The patient is a female aged 30–39. The photograph is a close-up of the affected area. The lesion involves the front of the torso:
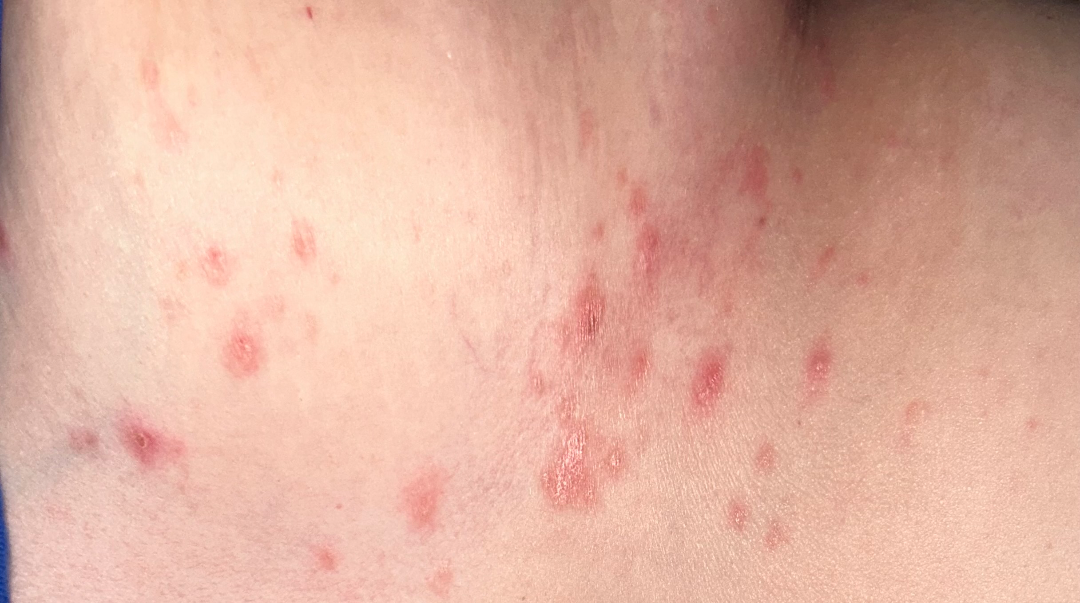The reviewing dermatologist was unable to assign a differential diagnosis from the image. The lesion is described as raised or bumpy. Present for less than one week. No associated systemic symptoms reported. Self-categorized by the patient as a rash. The lesion is associated with itching, burning and bothersome appearance.